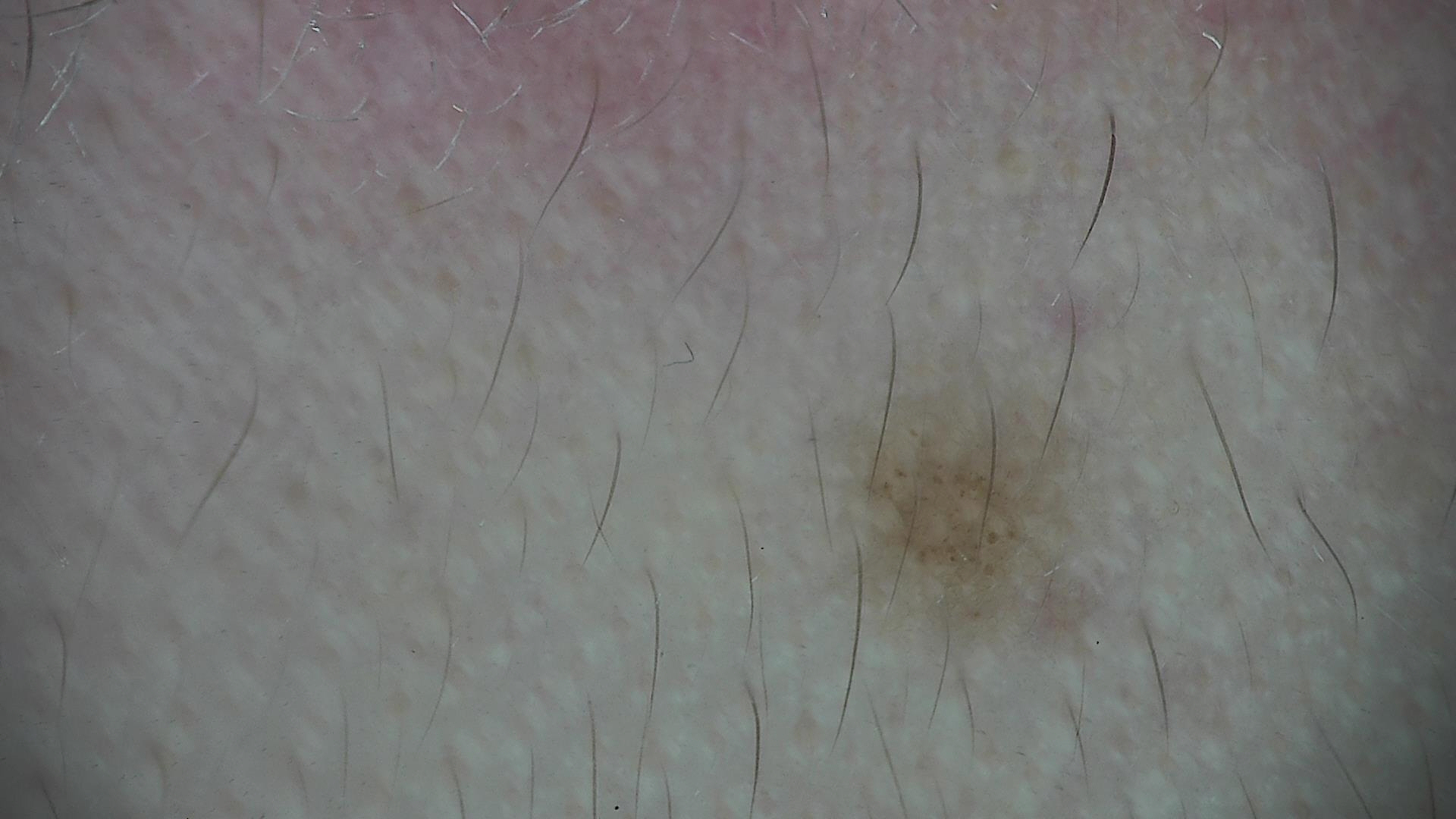The diagnostic label was a Miescher nevus.